A smartphone photograph of a skin lesion · the patient is Fitzpatrick phototype III: 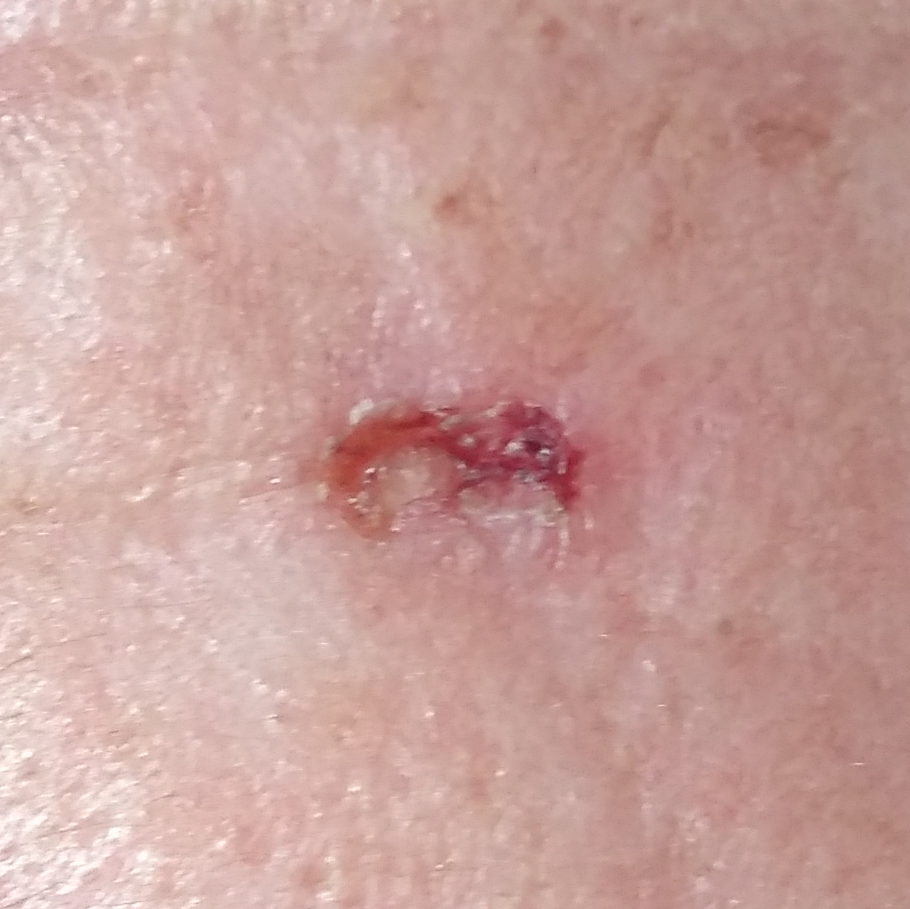The lesion is located on the face. The patient reports that the lesion is elevated, but does not hurt. The biopsy diagnosis was a malignant skin lesion — a basal cell carcinoma.